A male subject, aged around 40 · a dermatoscopic image of a skin lesion.
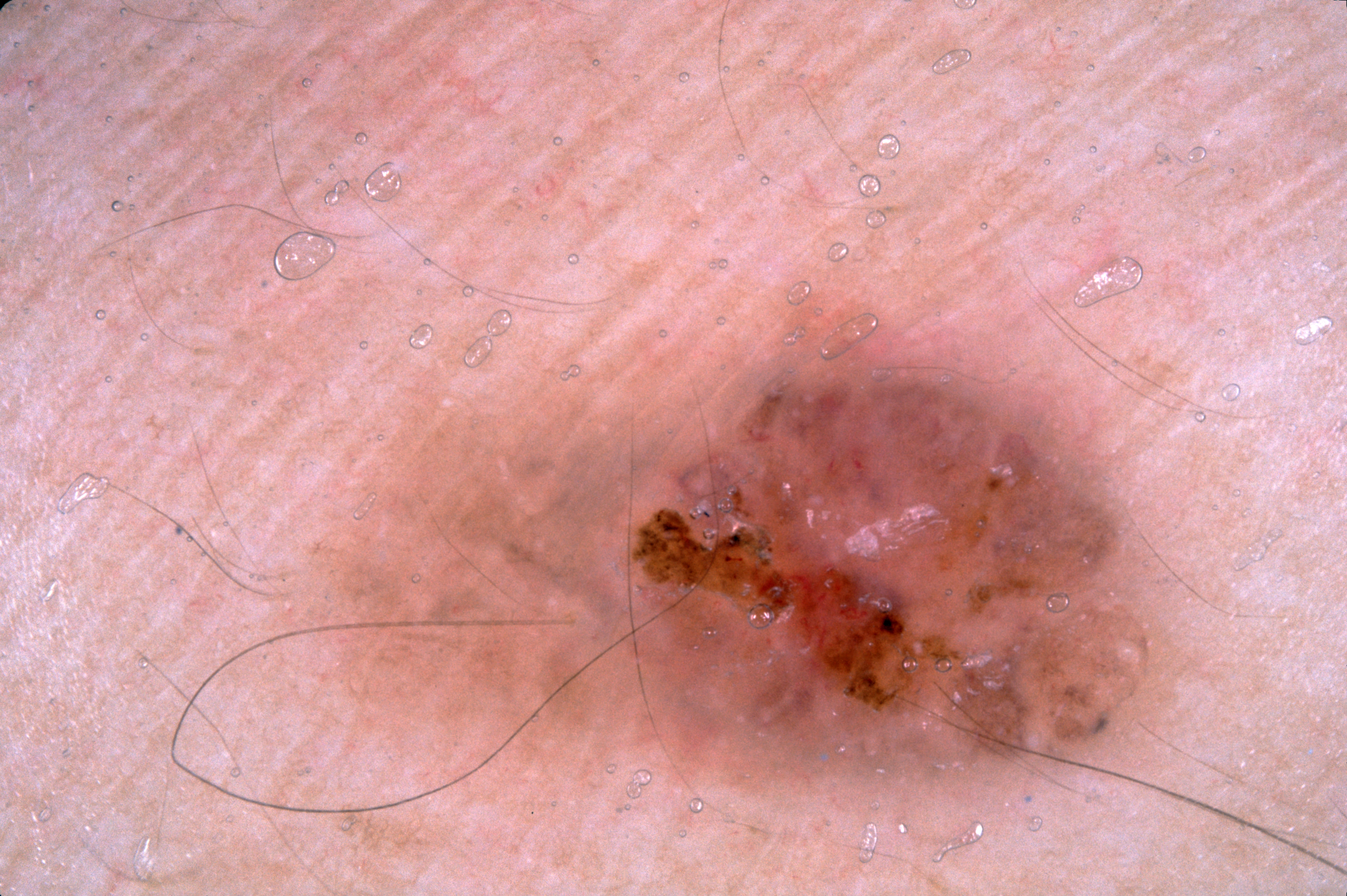absent dermoscopic findings: streaks, negative network, pigment network, and milia-like cysts
bounding box: x1=300 y1=291 x2=1186 y2=802
impression: a melanoma, a malignant lesion